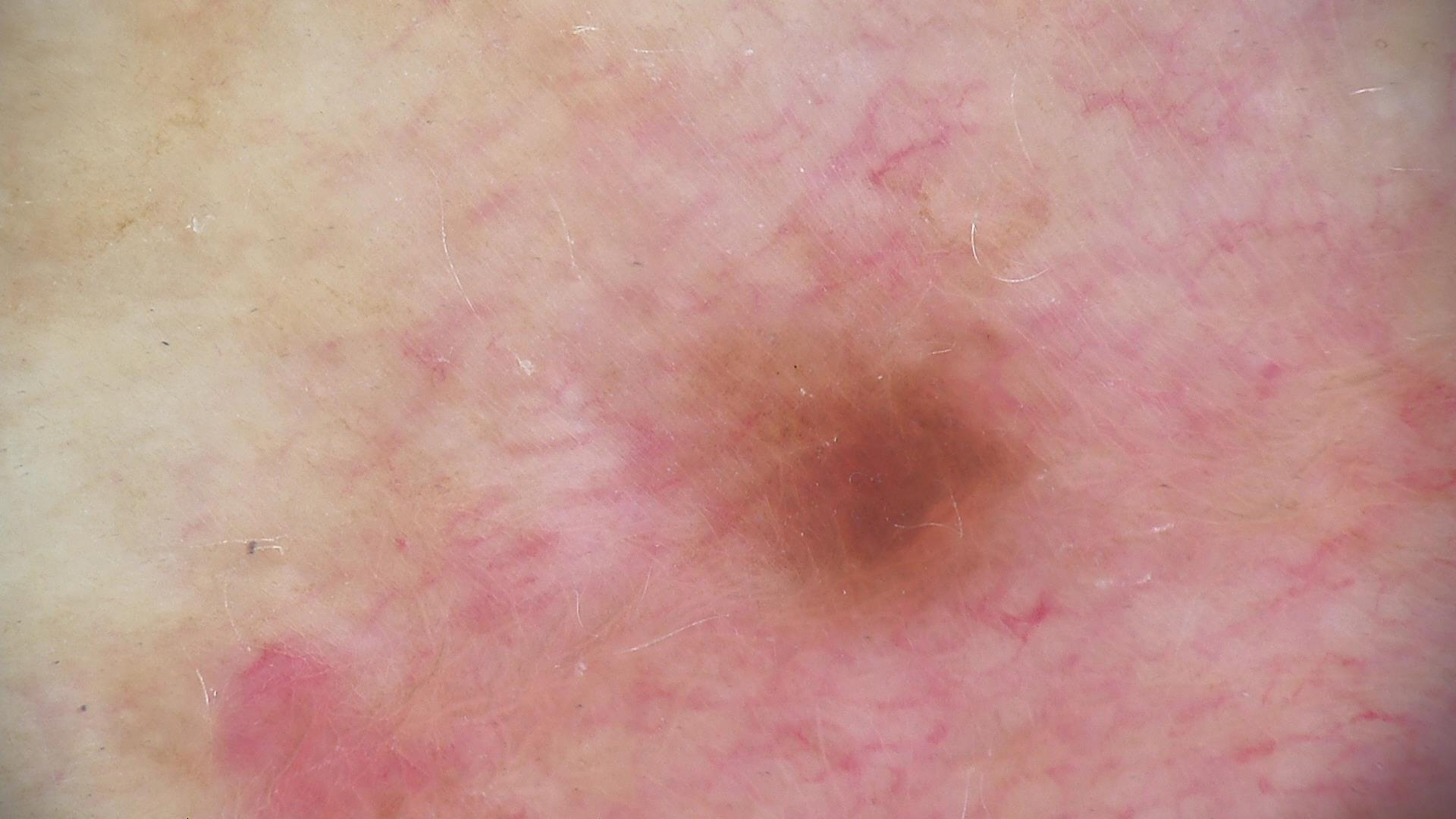A dermoscopic image of a skin lesion. The diagnostic label was a dysplastic junctional nevus.